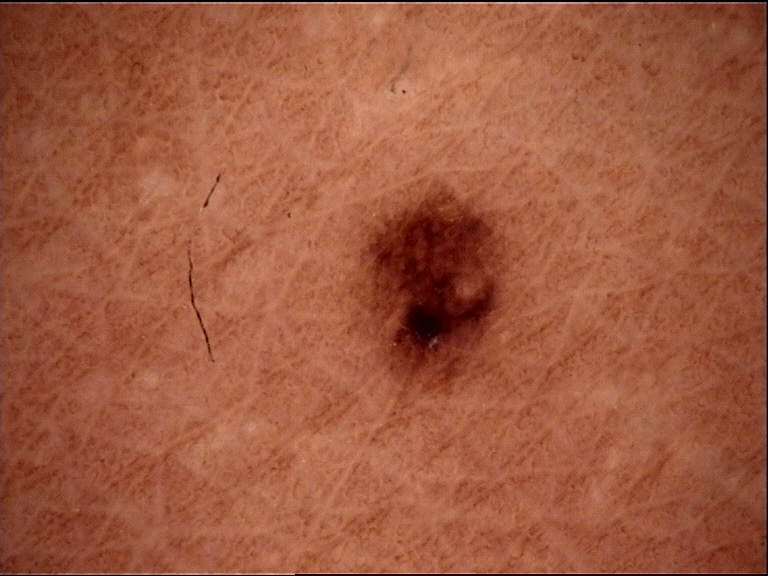Q: What was the diagnostic impression?
A: dysplastic junctional nevus (expert consensus)